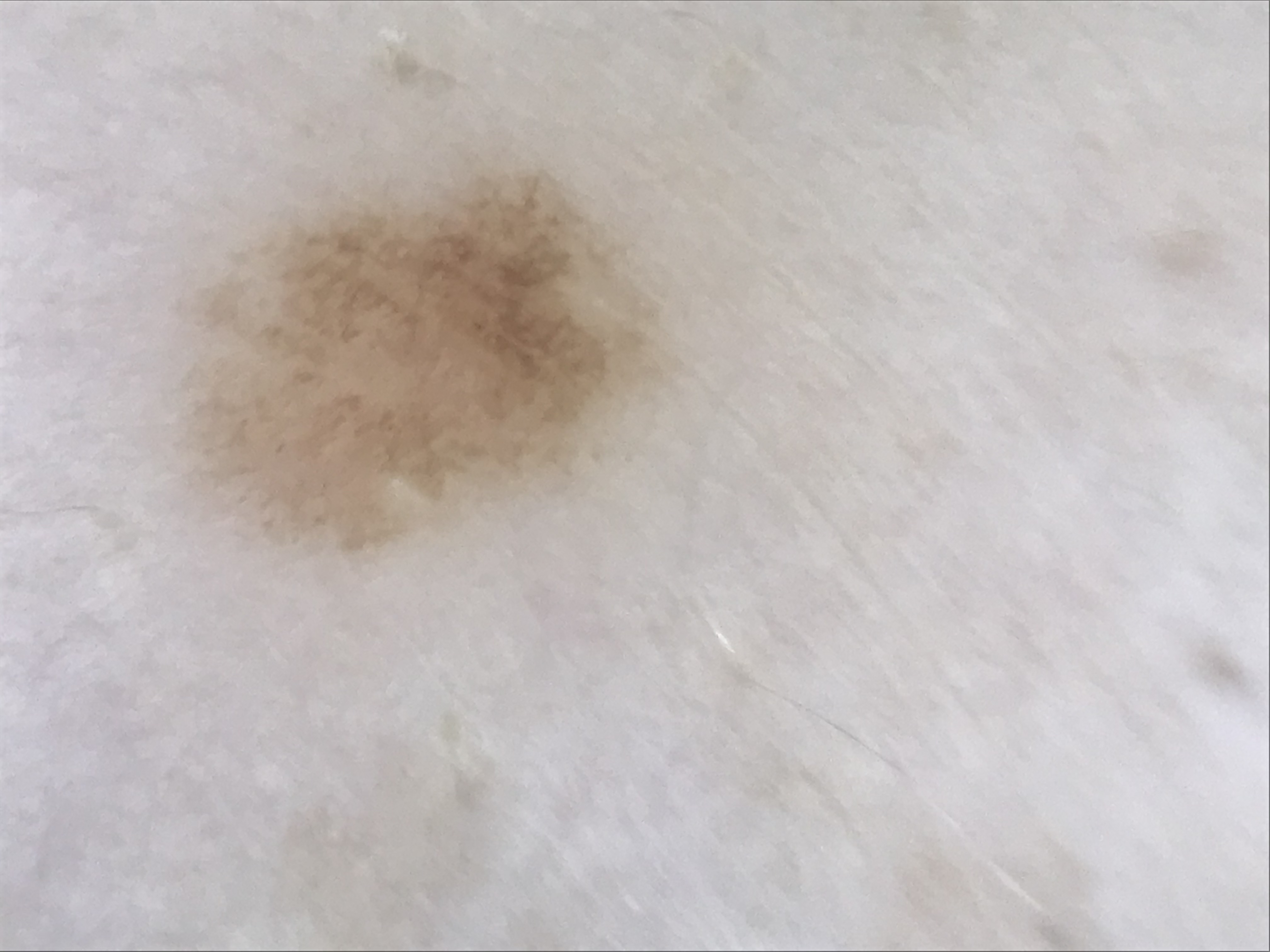Consistent with a junctional nevus.